A close-up photograph · female patient, age 18–29 · located on the arm:
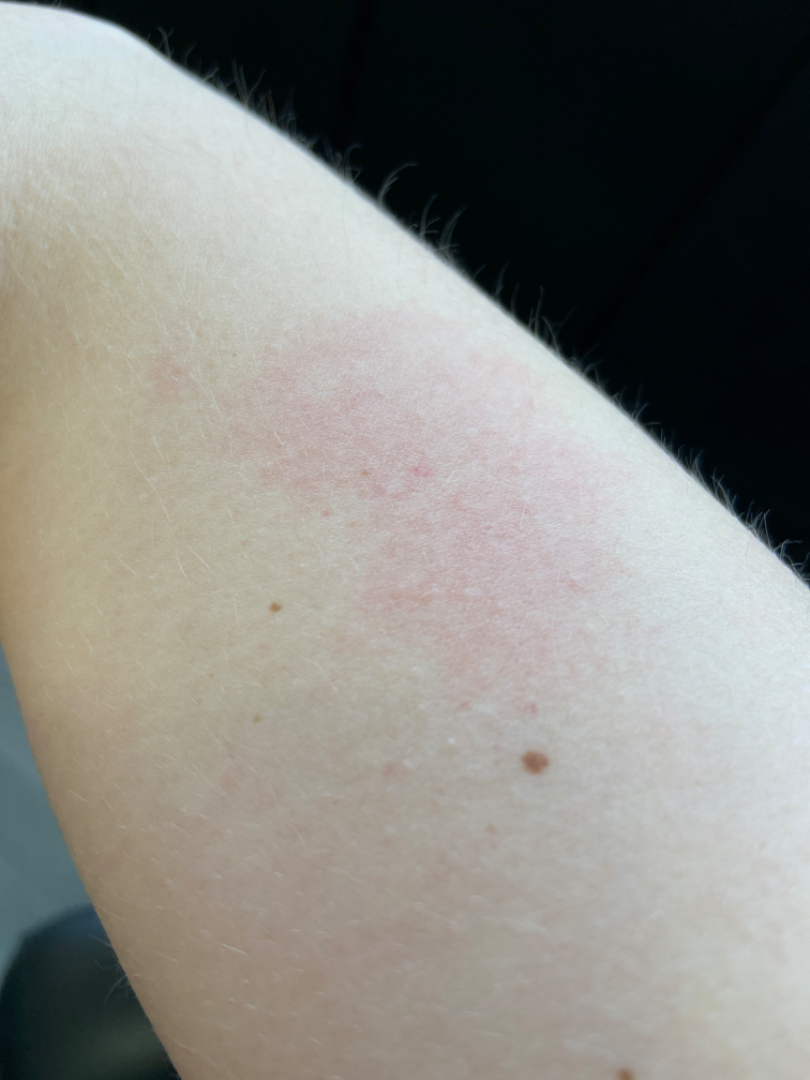{"differential": ["Eczema", "Acute dermatitis, NOS"]}